A male patient aged around 65; this is a dermoscopic photograph of a skin lesion — 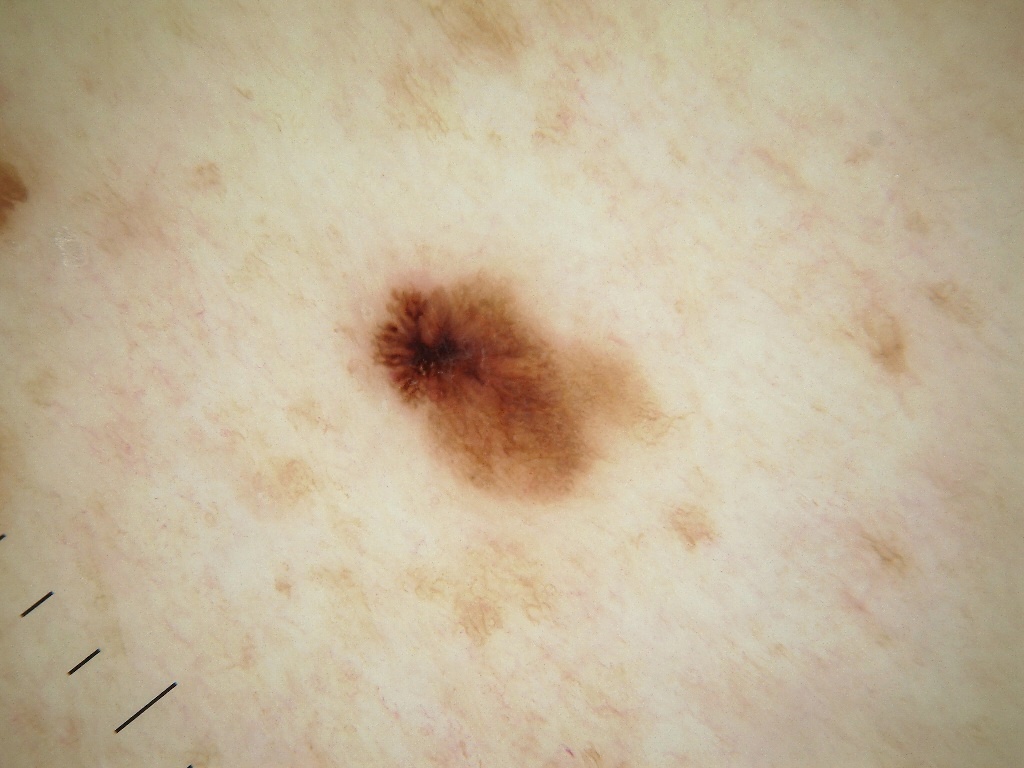{"lesion_extent": "small", "dermoscopic_features": {"present": ["pigment network"], "absent": ["globules", "milia-like cysts", "negative network", "streaks"]}, "lesion_location": {"bbox_xyxy": [359, 257, 658, 507]}, "diagnosis": {"name": "melanoma", "malignancy": "malignant", "lineage": "melanocytic", "provenance": "histopathology"}}